A clinical photograph of a skin lesion. A female patient in their early 70s:
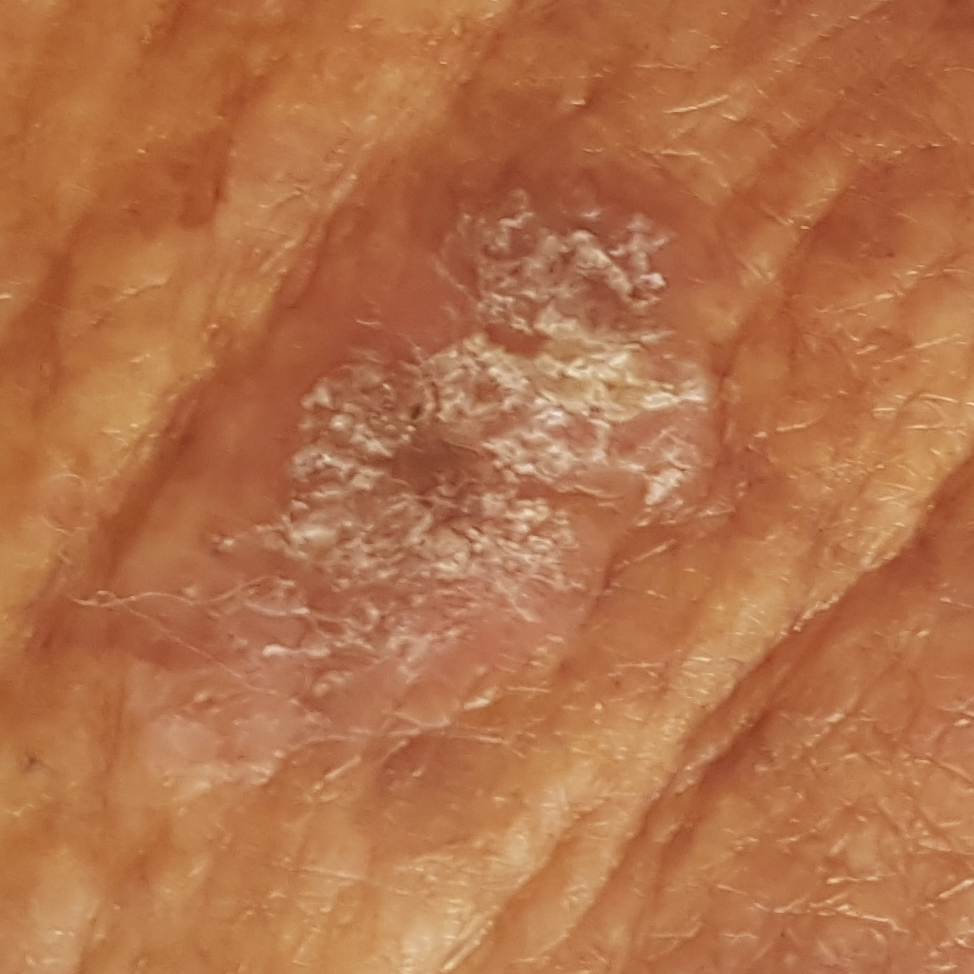region=the face; reported symptoms=elevation, itching; pathology=actinic keratosis (biopsy-proven).